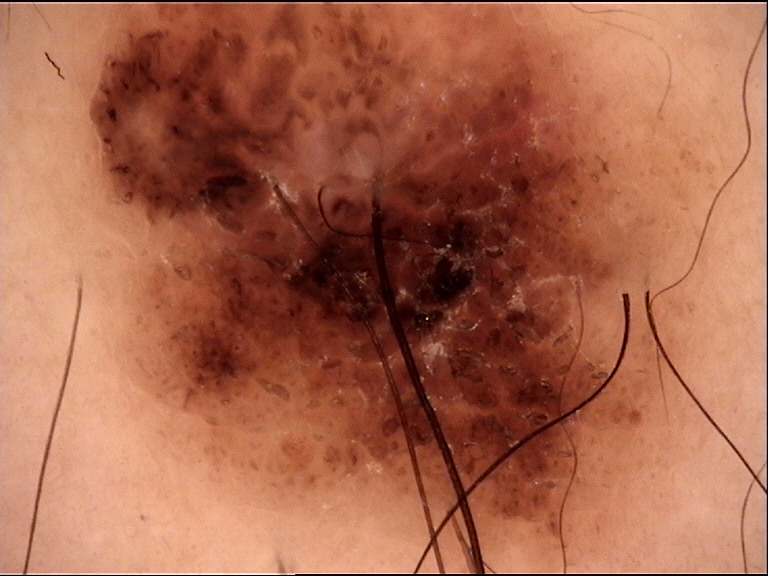Case: Dermoscopy of a skin lesion. Impression: Classified as a dysplastic compound nevus.